The subject is a female in their mid-20s; dermoscopy of a skin lesion:
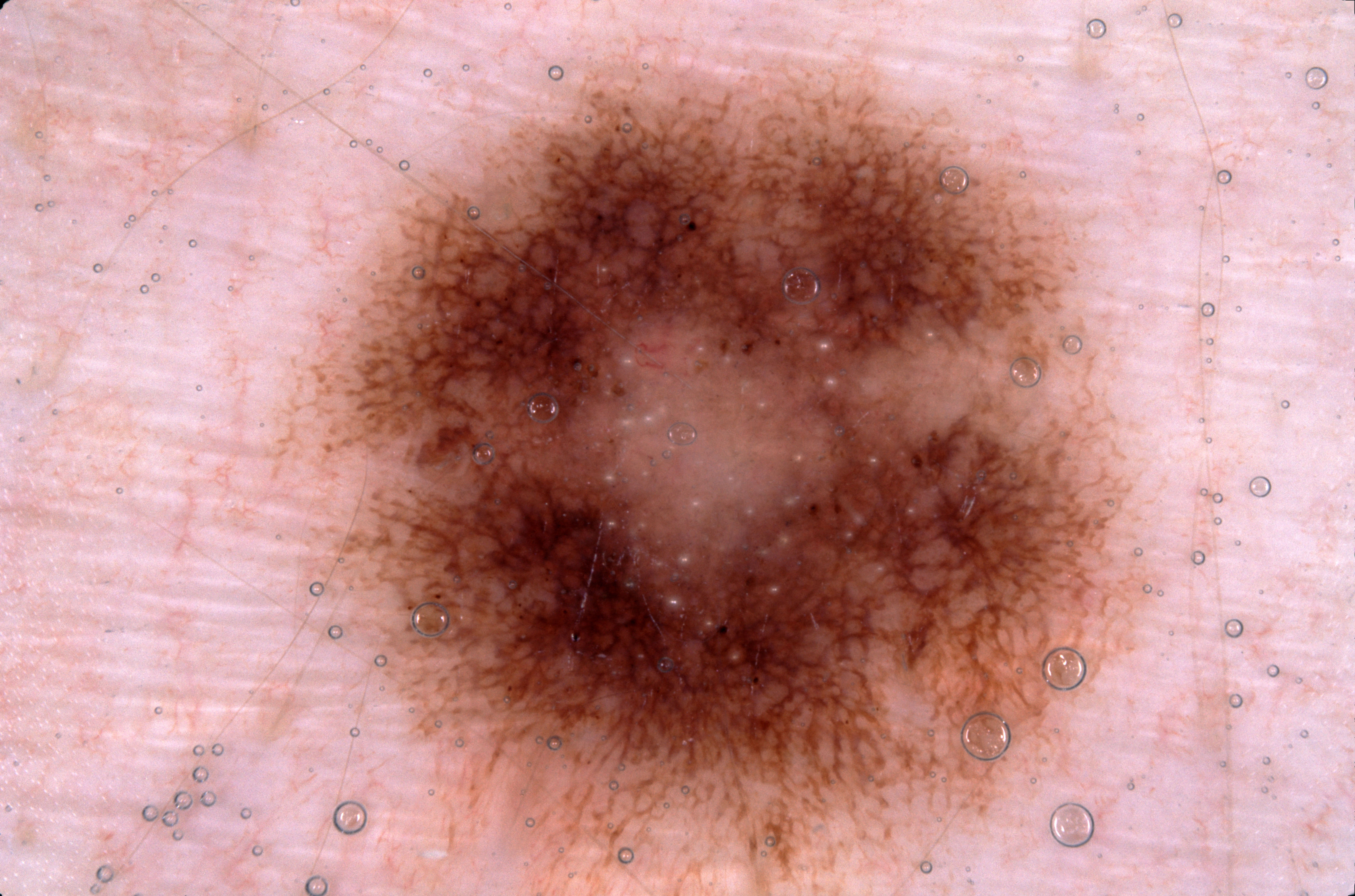Dermoscopic assessment notes pigment network and milia-like cysts. The lesion spans left=284, top=40, right=1166, bottom=891. A large lesion occupying much of the field. Consistent with a melanocytic nevus.